A female subject 32 years old · a dermatoscopic image of a skin lesion · imaged for a research study, with no referral diagnosis recorded:
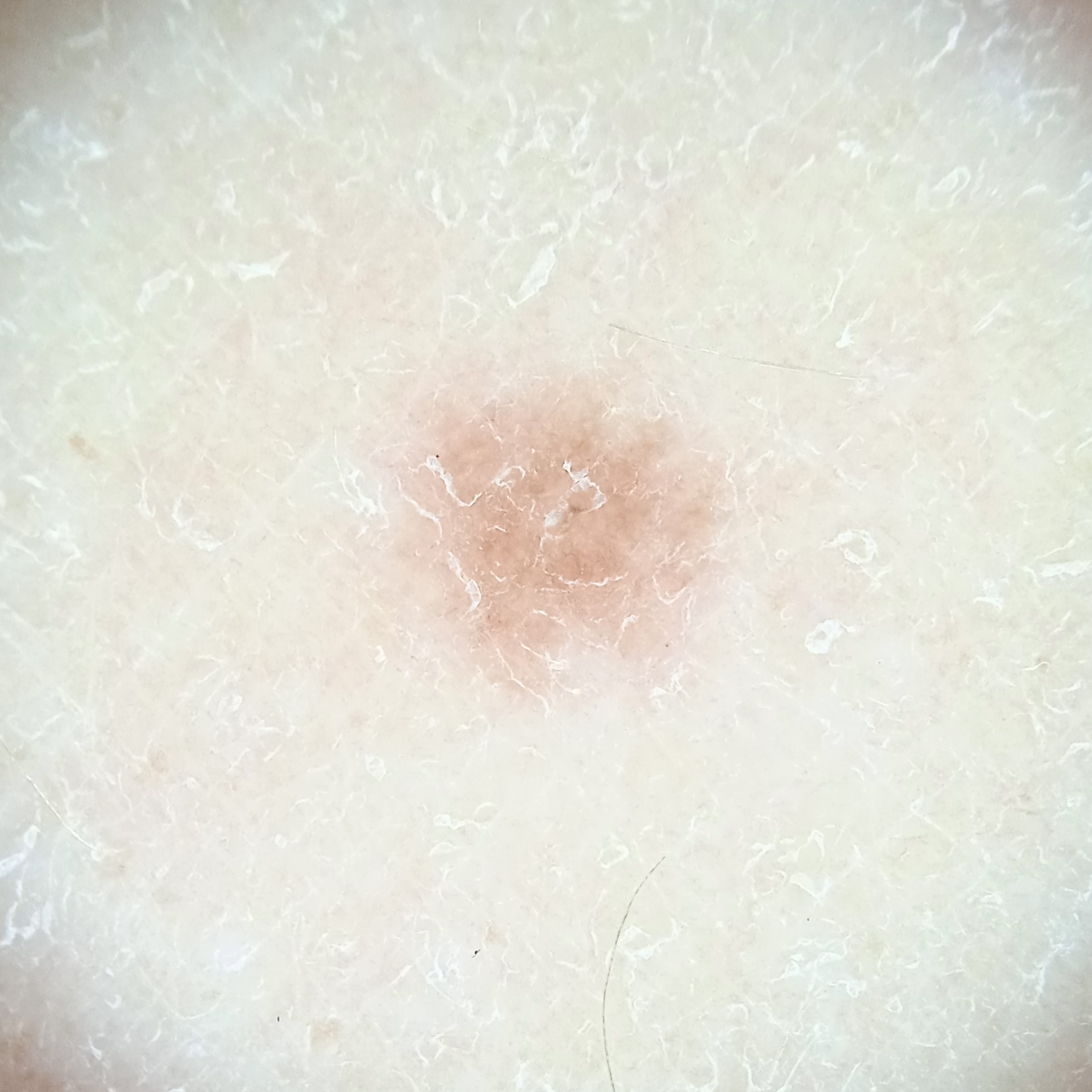The lesion is located on a leg. Measuring roughly 4.1 mm. Dermatologist review favored a melanocytic nevus.